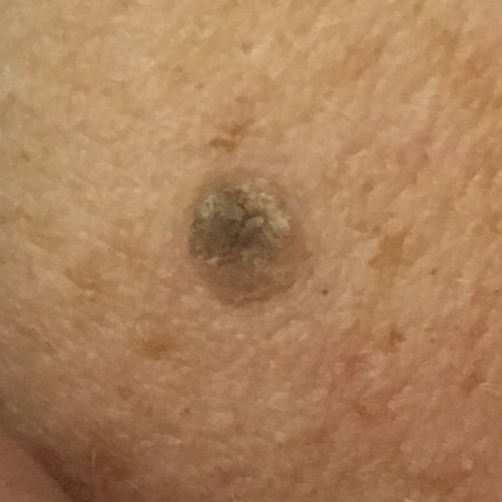Findings:
A subject age 39. A clinical photograph showing a skin lesion. The lesion is on the back. The patient reports that the lesion has grown, but does not hurt and has not bled.
Impression:
Expert review favored a benign skin lesion — a seborrheic keratosis.